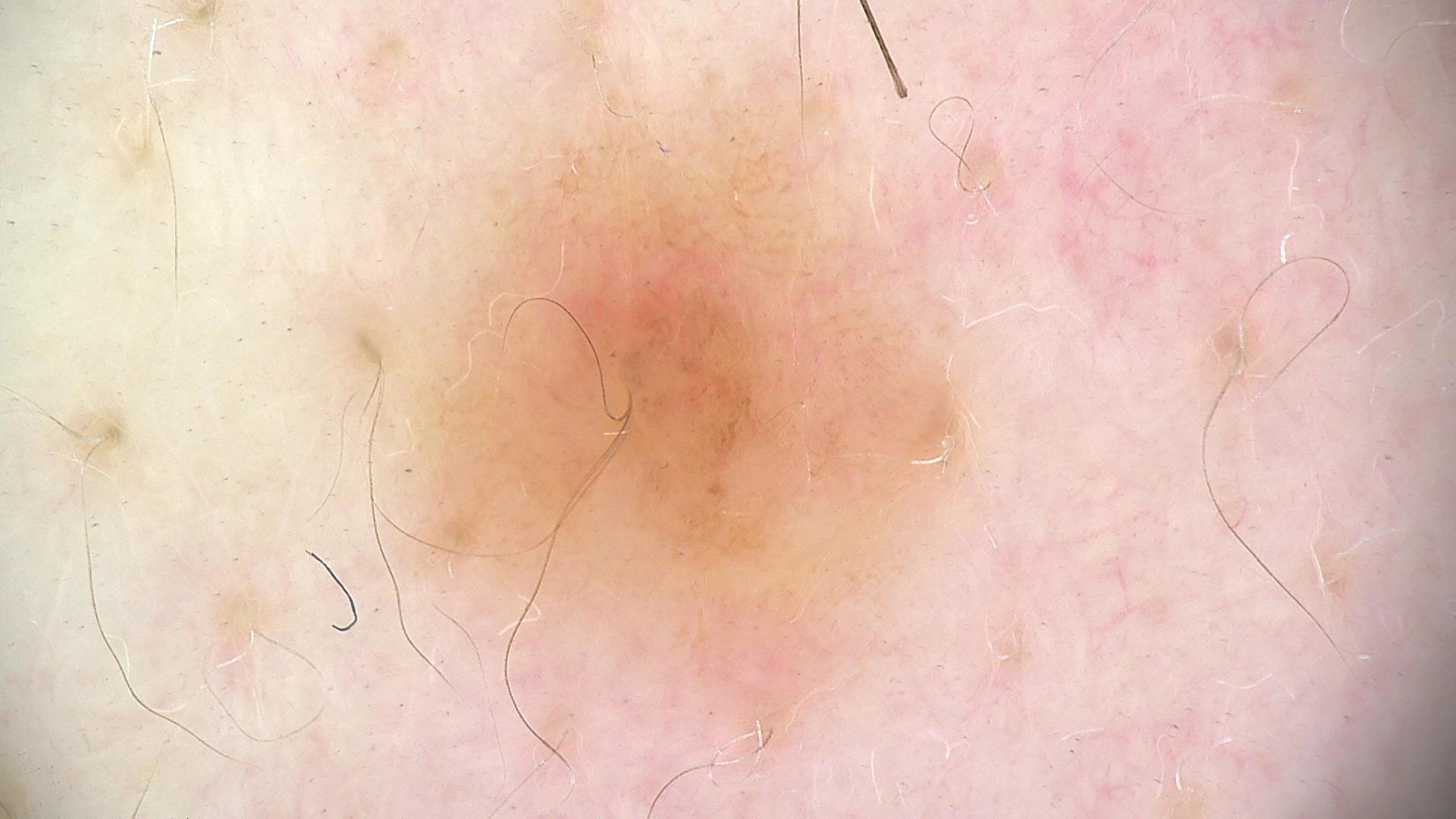diagnostic label: junctional nevus (expert consensus).